A dermoscopic image of a skin lesion: 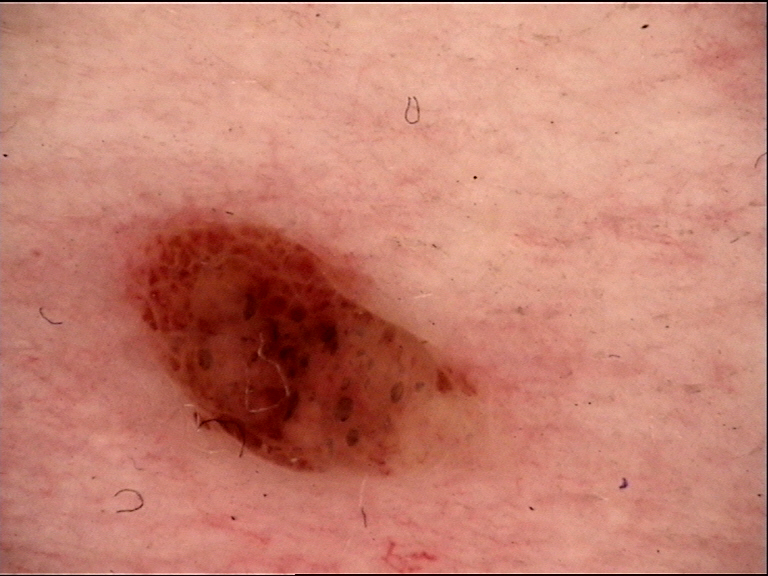diagnosis:
  name: compound nevus
  code: cb
  malignancy: benign
  super_class: melanocytic
  confirmation: expert consensus